A clinical photo of a skin lesion taken with a smartphone. The patient was assessed as skin type I. A male patient 75 years old. The chart records alcohol use, tobacco use, pesticide exposure, prior skin cancer (patient or family), and no prior malignancy (patient or family): 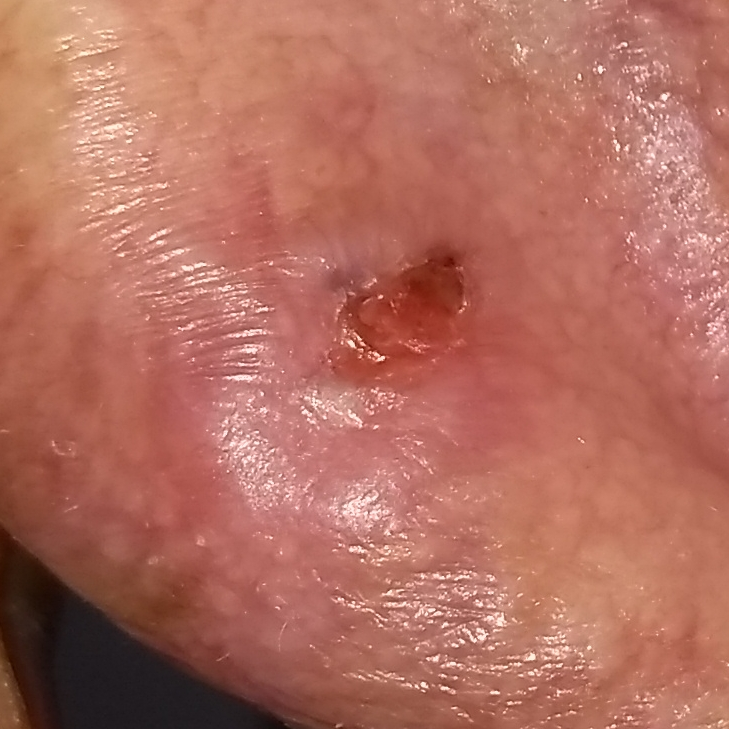Case summary:
The lesion involves an ear. The lesion measures 5 × 4 mm.
Conclusion:
Histopathologically confirmed as a basal cell carcinoma.